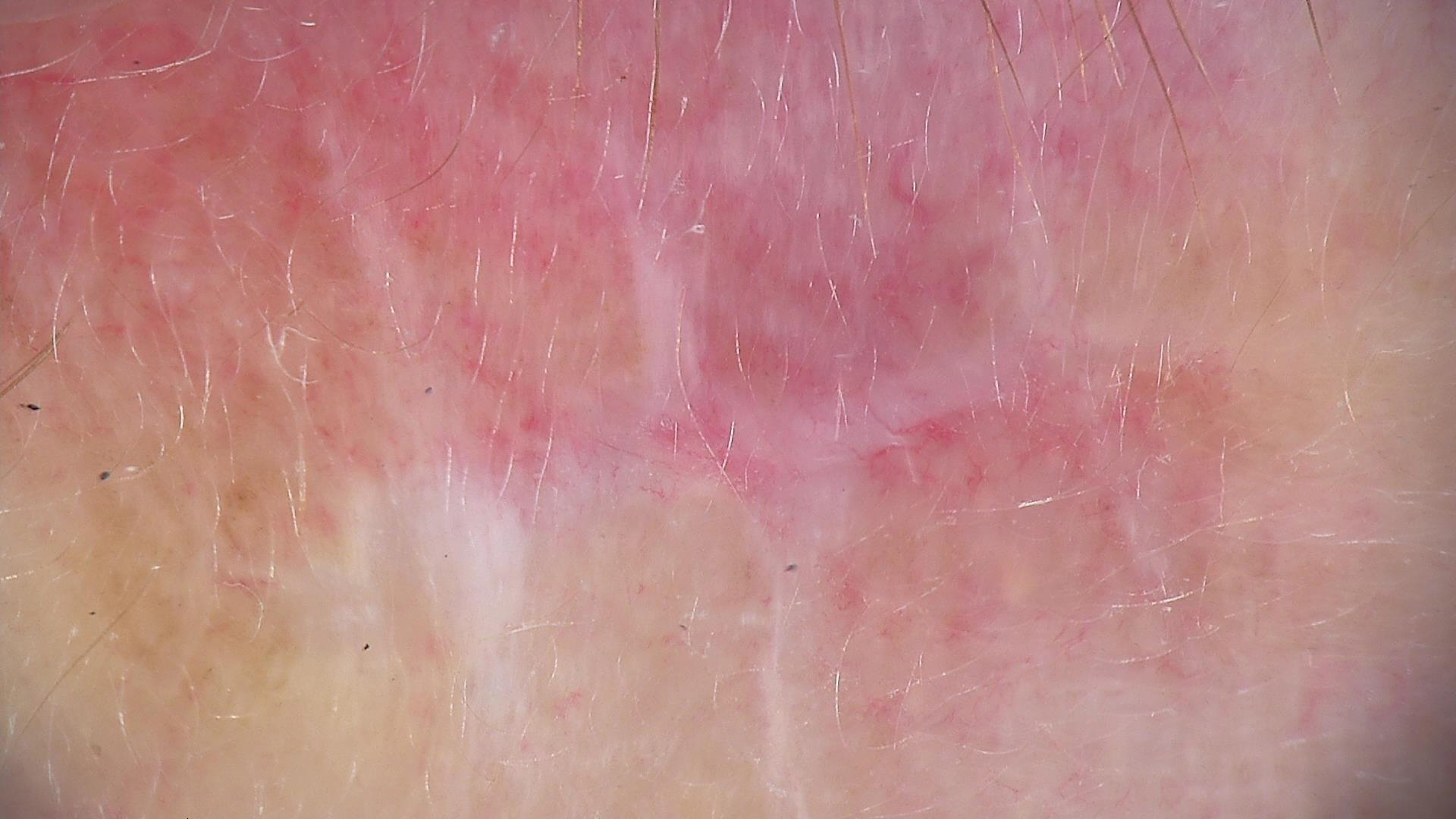Summary:
A dermoscopic image of a skin lesion.
Conclusion:
The biopsy diagnosis was a keratinocytic lesion — a basal cell carcinoma.